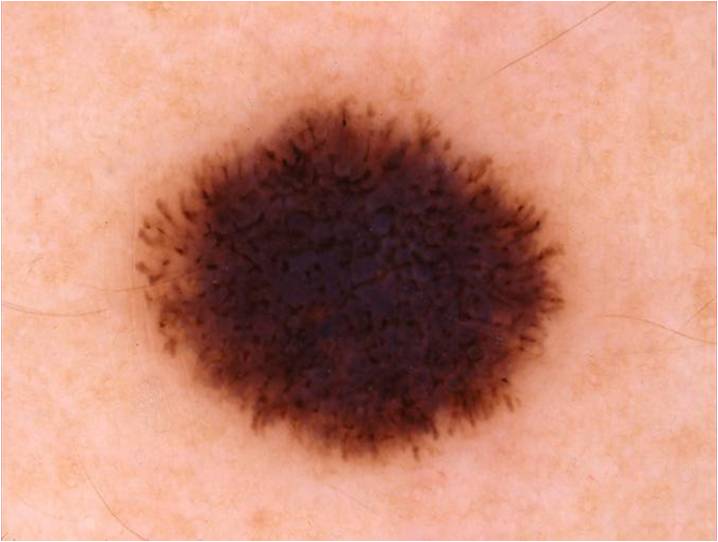modality: dermoscopy
subject: male, aged 18 to 22
lesion bbox: x1=135 y1=92 x2=567 y2=462
dermoscopic findings: pigment network, streaks, and globules
diagnosis: a melanocytic nevus